A patient age 66; a smartphone photograph of a skin lesion.
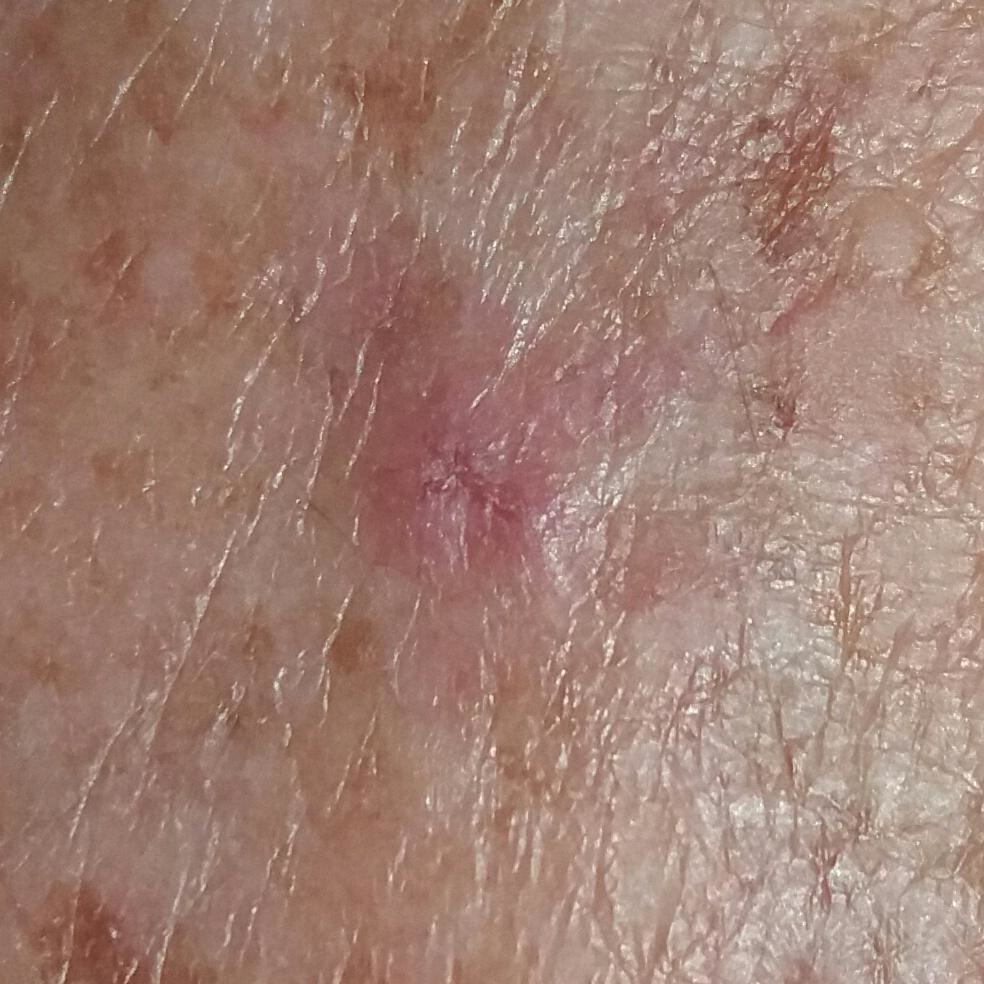Located on a hand.
Clinically diagnosed as an actinic keratosis.